A male patient approximately 60 years of age; the patient is skin type III; a dermatoscopic image of a skin lesion — 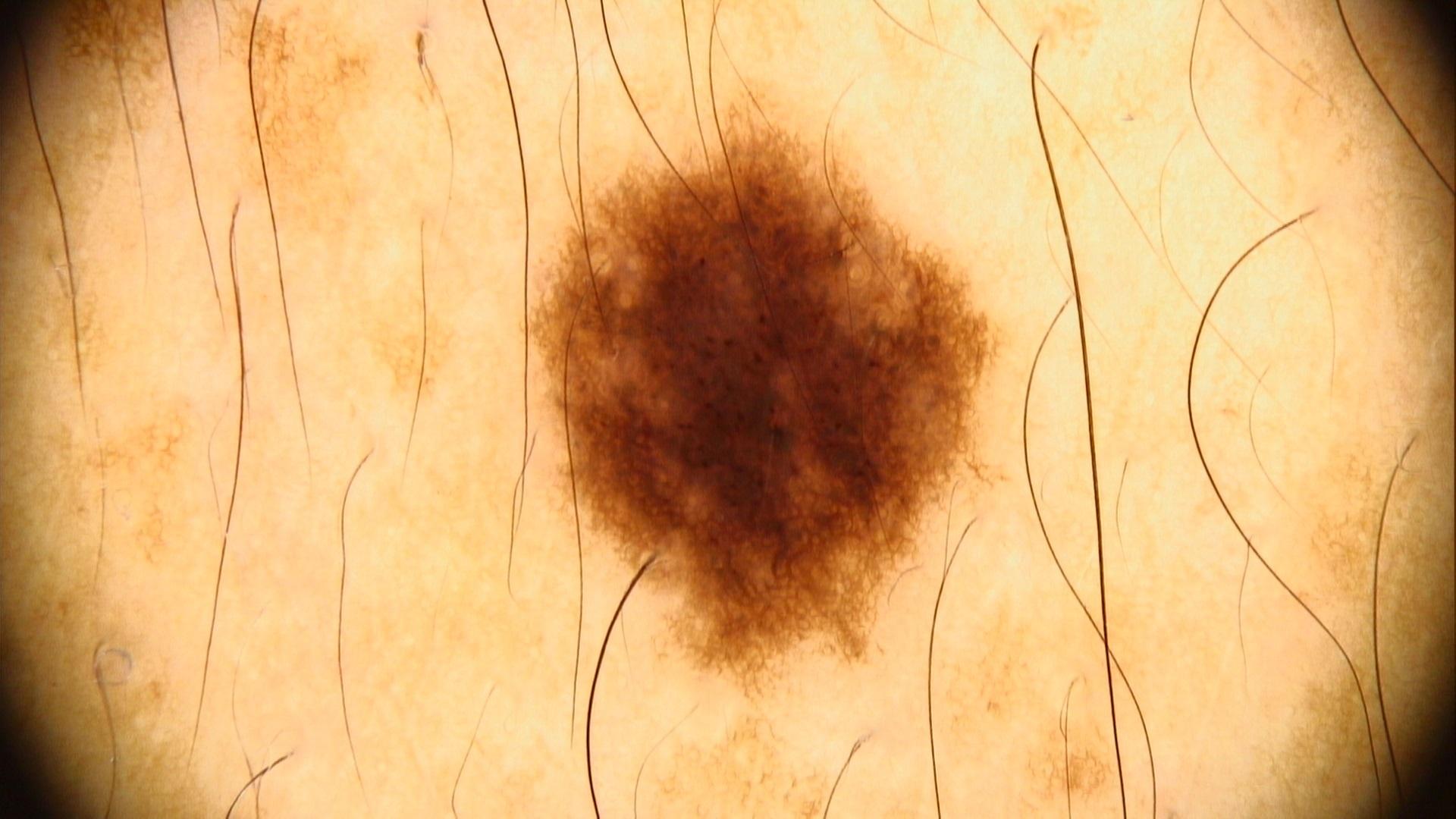  diagnosis:
    name: Nevus
    malignancy: benign
    confirmation: expert clinical impression
    lineage: melanocytic